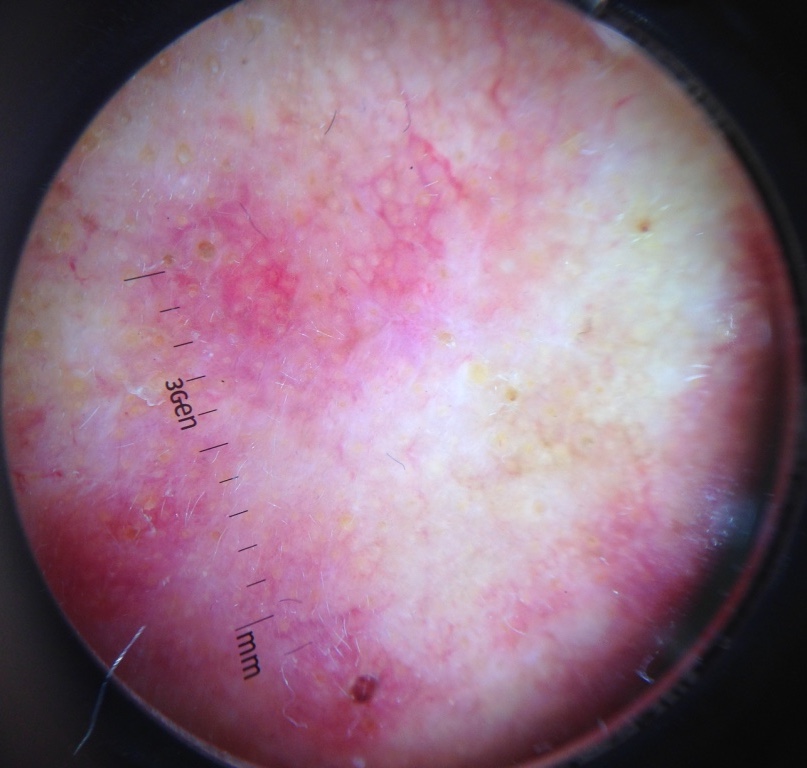A dermoscopic close-up of a skin lesion. The morphology is that of a keratinocytic lesion. Consistent with a lesion of indeterminate malignant potential — an actinic keratosis.